A clinical close-up photograph of a skin lesion. A male patient aged 66 — 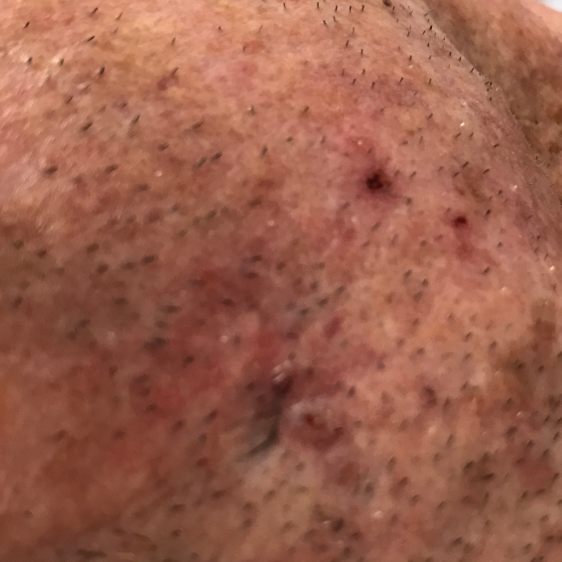The lesion involves a foot.
The patient describes that the lesion is elevated and itches.
Histopathologically confirmed as a squamous cell carcinoma.